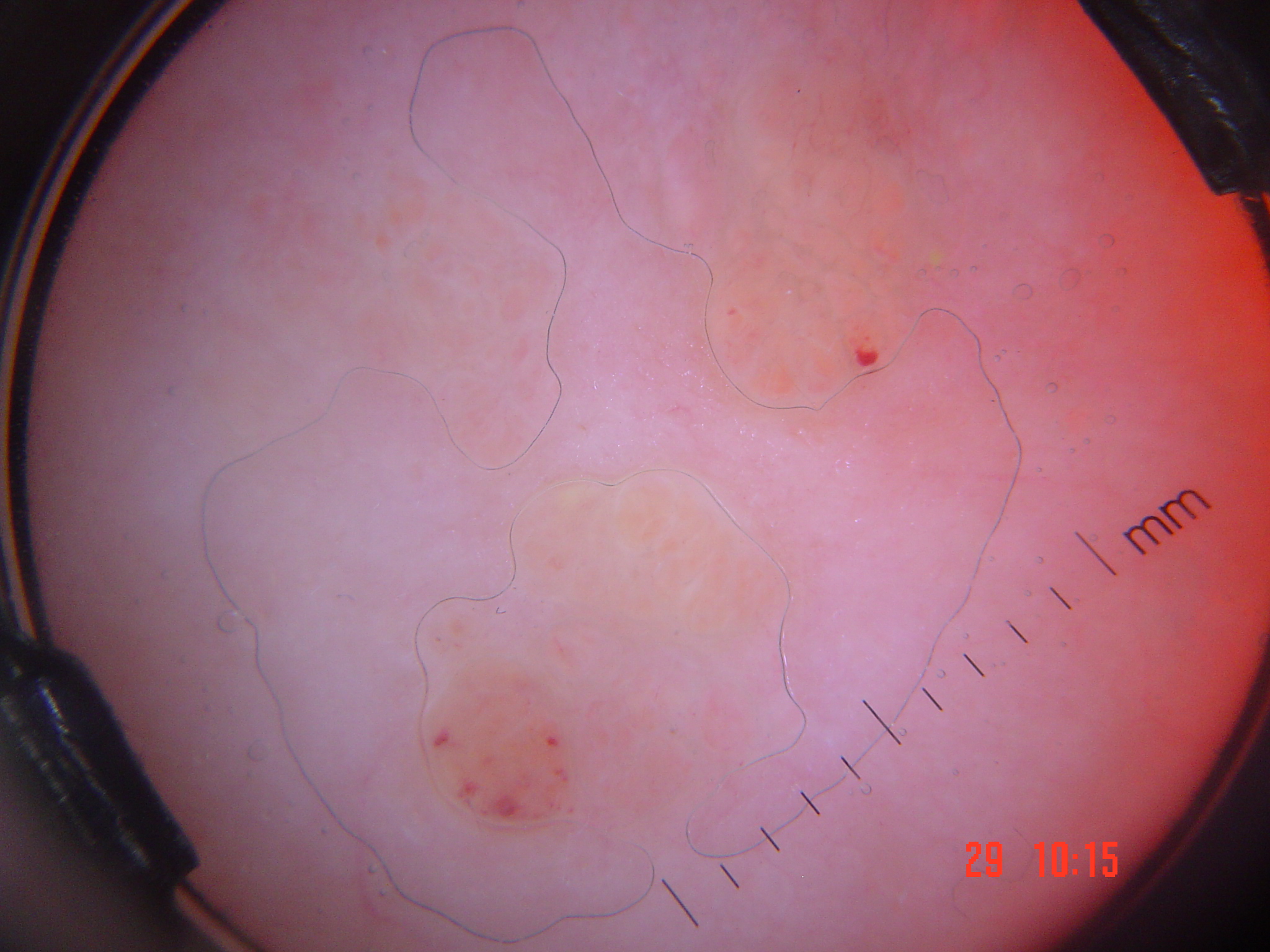A dermatoscopic image of a skin lesion. This is a vascular lesion. The diagnosis was a lymphangioma.